A dermoscopic photograph of a skin lesion:
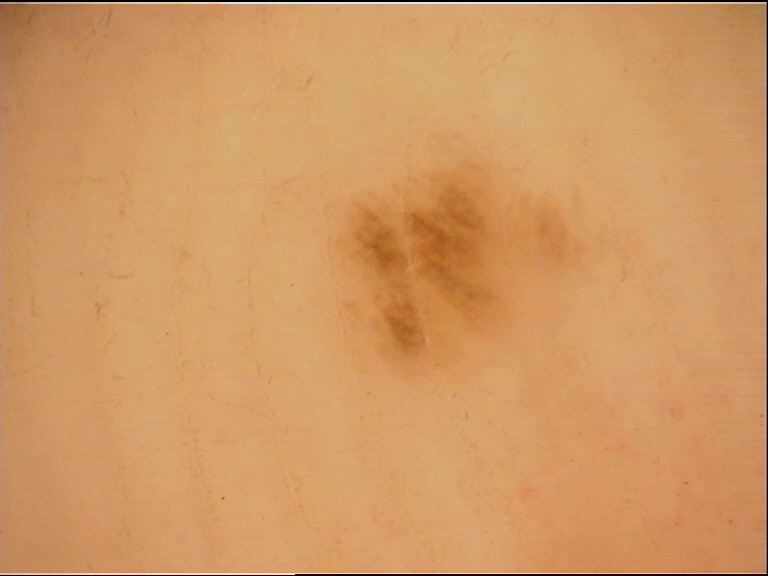The architecture is that of a banal lesion.
Consistent with an acral junctional nevus.